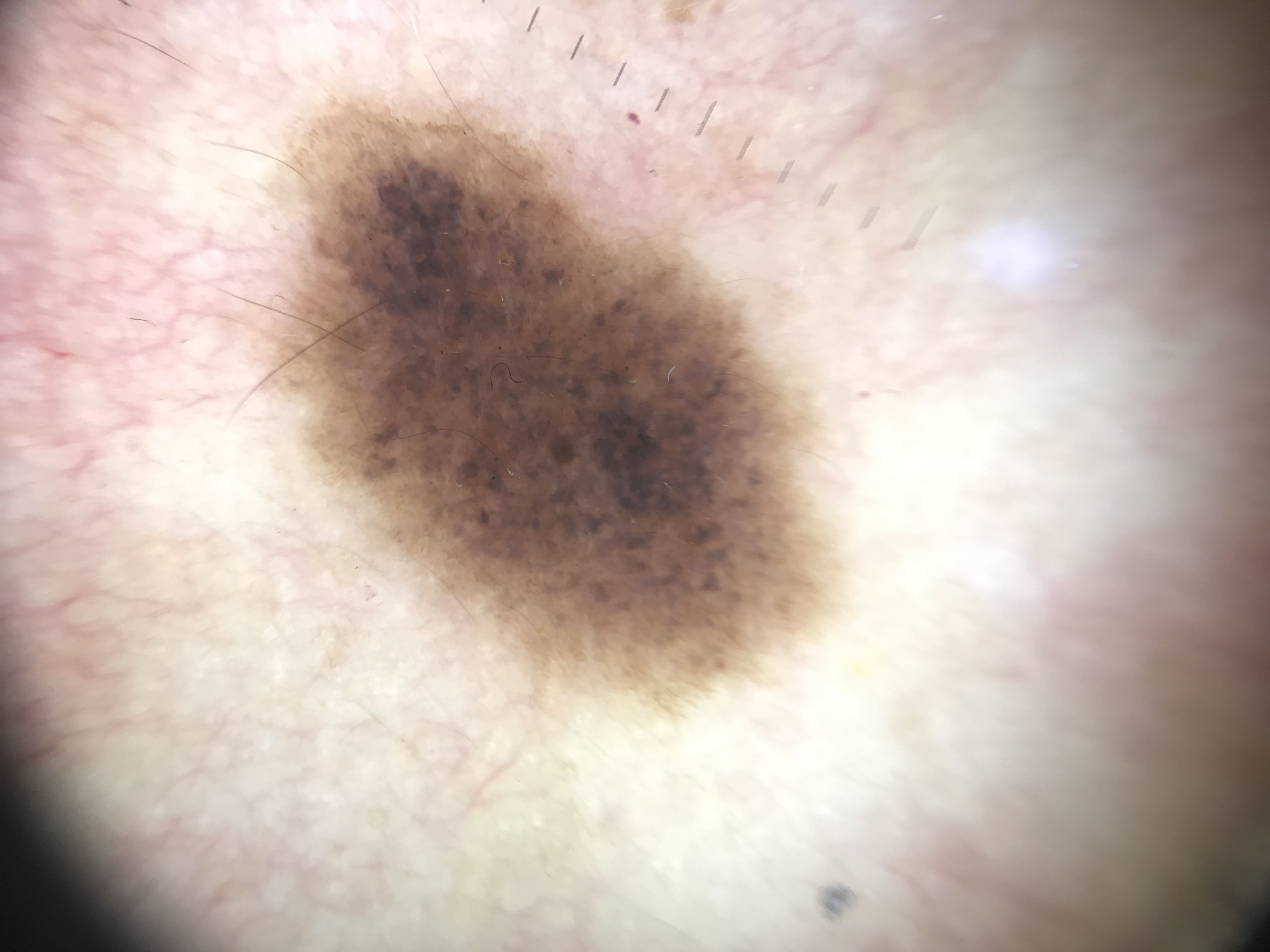Findings: A dermoscopic close-up of a skin lesion. The morphology is that of a banal lesion. Impression: Diagnosed as a congenital compound nevus.